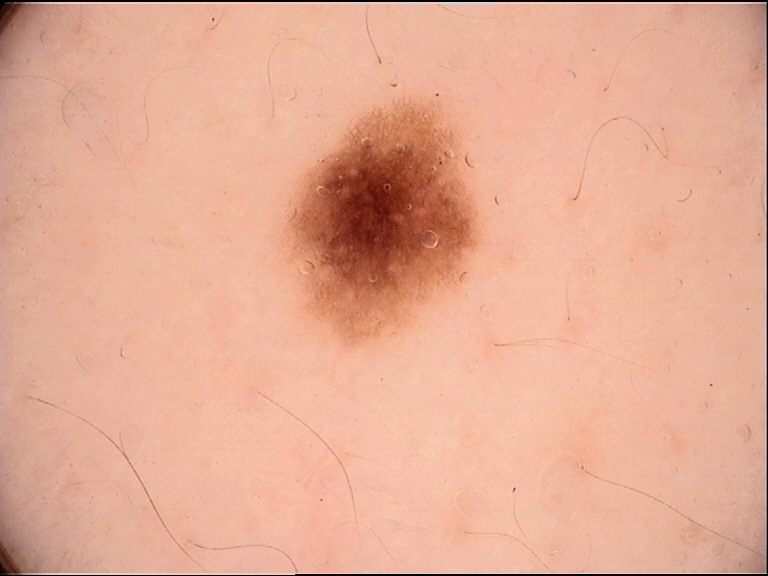Conclusion:
Classified as a benign lesion — a dysplastic junctional nevus.